The photograph is a close-up of the affected area · the contributor is a female aged 40–49 · the affected area is the arm, leg and back of the torso: 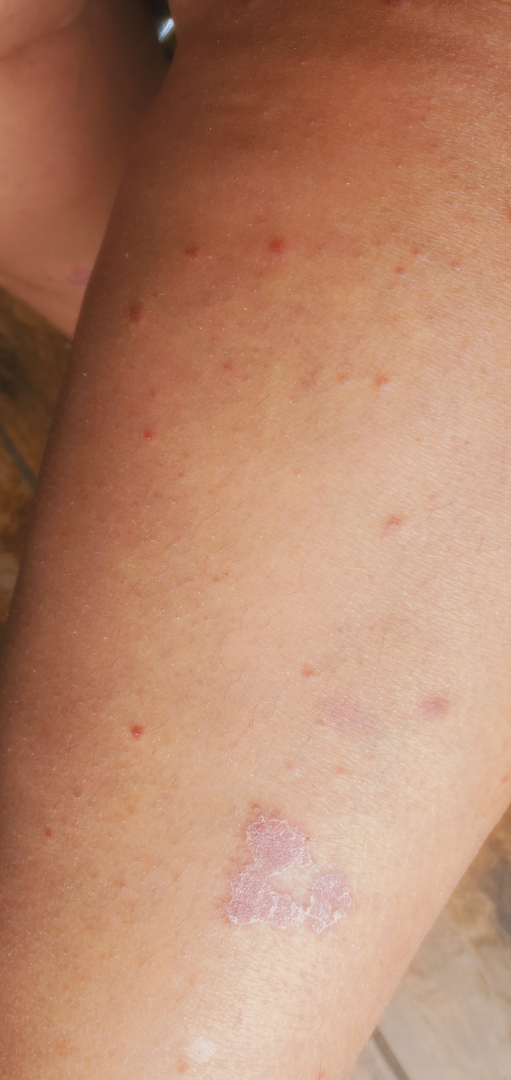onset: one to three months | patient's own categorization: a rash | described texture: rough or flaky | associated systemic symptoms: fatigue and joint pain | reported symptoms: enlargement, itching, bothersome appearance and bleeding | differential: Psoriasis (most likely); Lichen planus/lichenoid eruption (considered); Porokeratosis (unlikely).